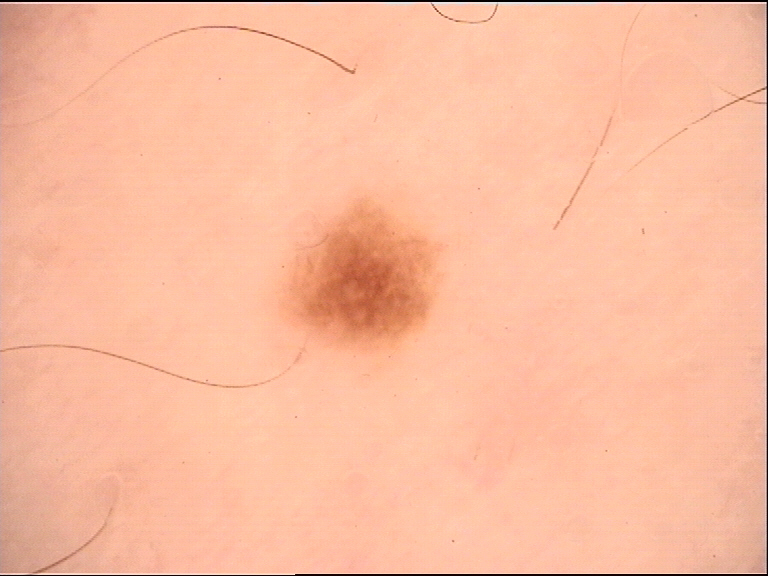modality: dermoscopy; diagnostic label: dysplastic junctional nevus (expert consensus).